Associated systemic symptoms include shortness of breath, chills, joint pain and fatigue · the photo was captured at an angle · the patient notes the lesion is rough or flaky and raised or bumpy · present for one to four weeks · the patient described the issue as a rash · skin tone: Fitzpatrick V · located on the back of the torso, front of the torso and head or neck: 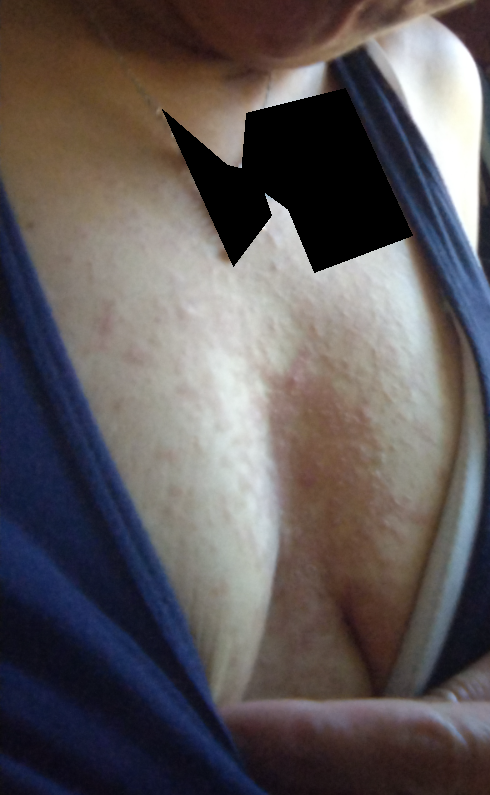  assessment: not assessable